A dermoscopic photograph of a skin lesion.
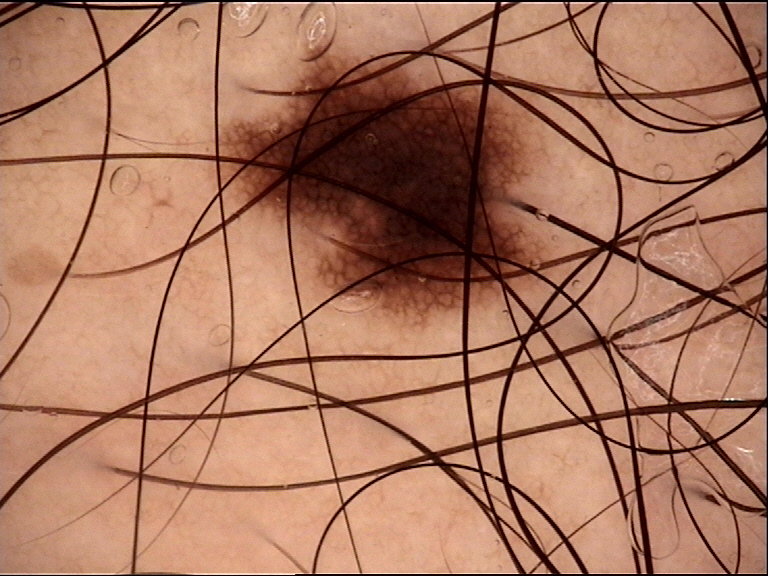label: junctional nevus (expert consensus)